A clinical photo of a skin lesion taken with a smartphone; recorded as Fitzpatrick phototype II.
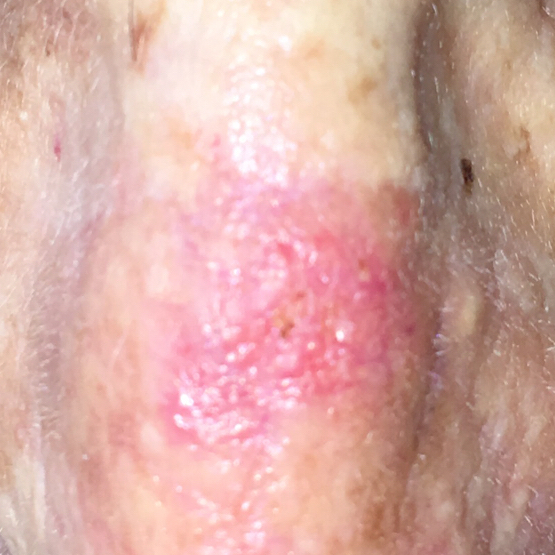The lesion measures approximately 13 × 11 mm. Per patient report, the lesion has bled, itches, and has grown. Biopsy-confirmed as a squamous cell carcinoma.